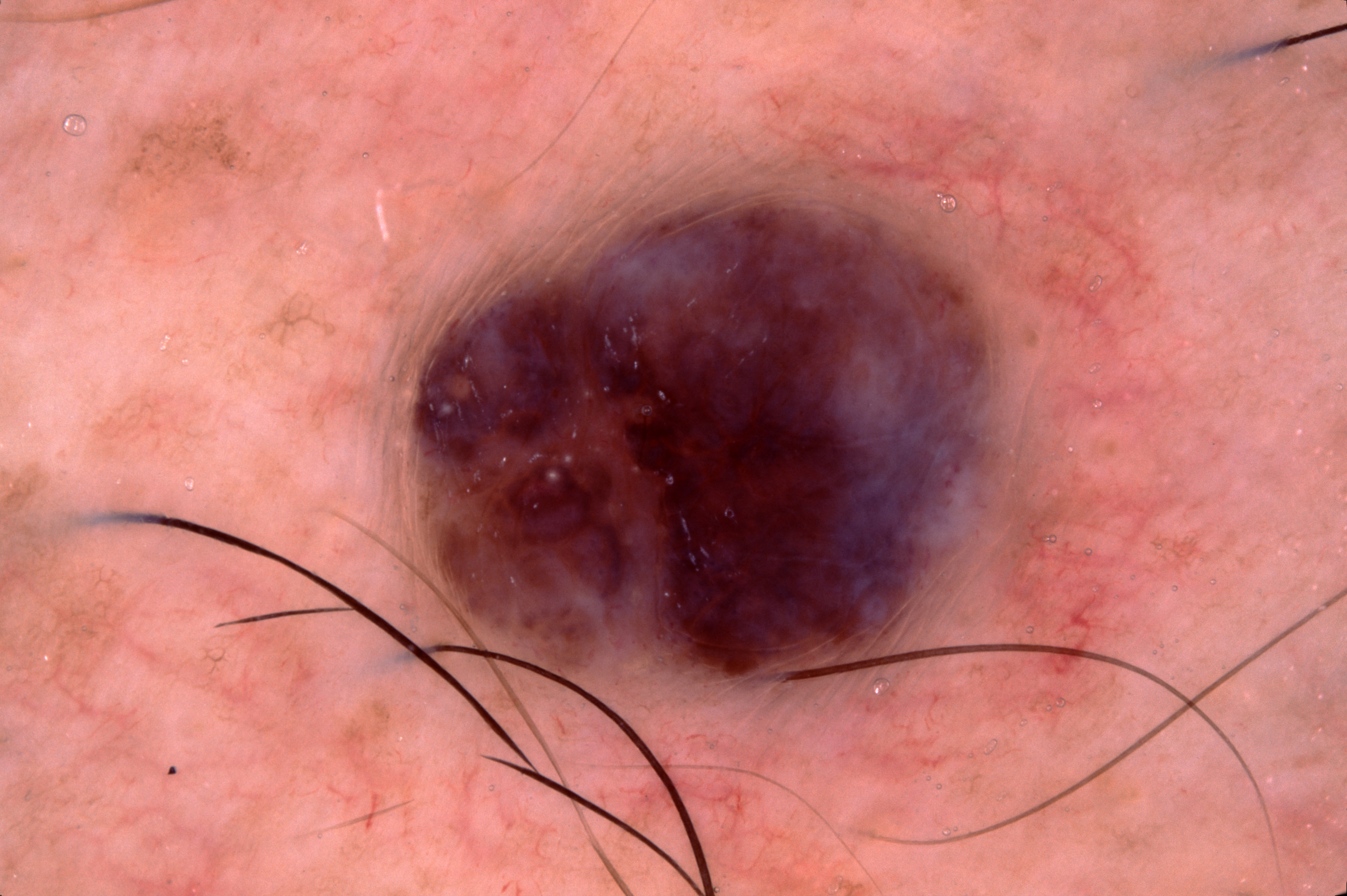patient — male, aged approximately 45 | imaging — dermoscopy of a skin lesion | dermoscopic features assessed but absent — milia-like cysts, streaks, negative network, and pigment network | lesion bbox — [349,103,1103,737] | diagnosis — a melanocytic nevus, a benign skin lesion.